The condition has been present for less than one week. An image taken at an angle. The arm is involved: 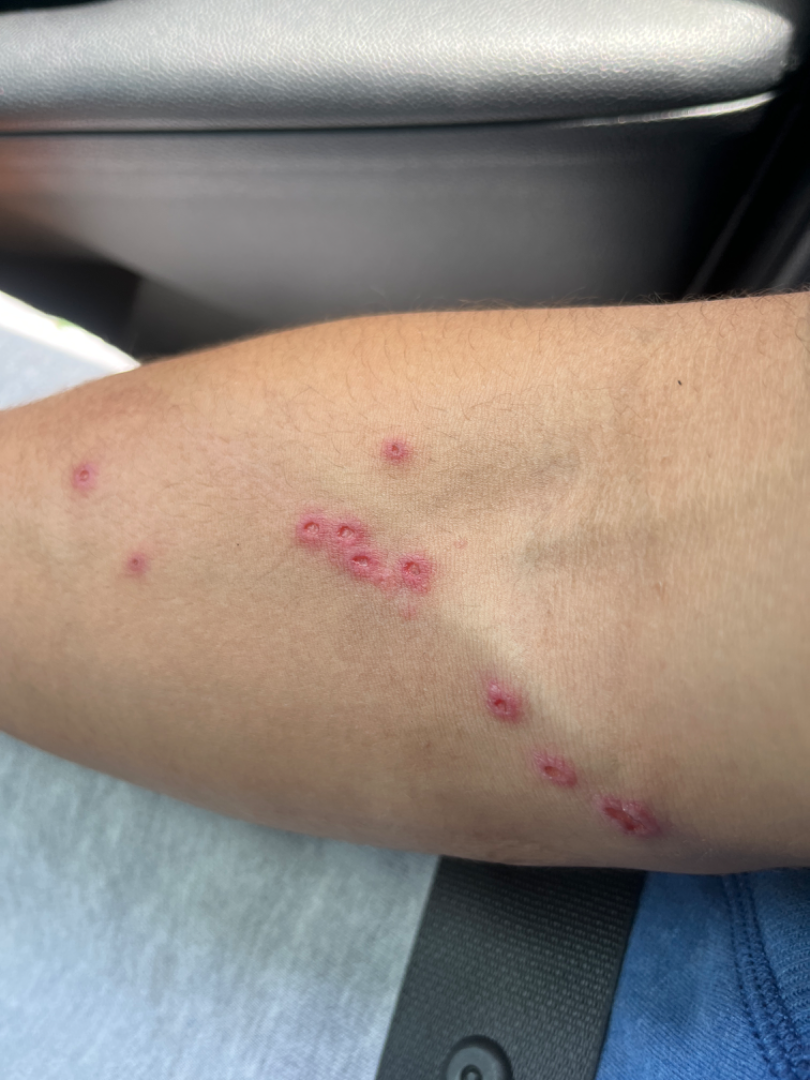  differential:
    leading:
      - Insect Bite
    considered:
      - Herpes Simplex
      - Allergic Contact Dermatitis